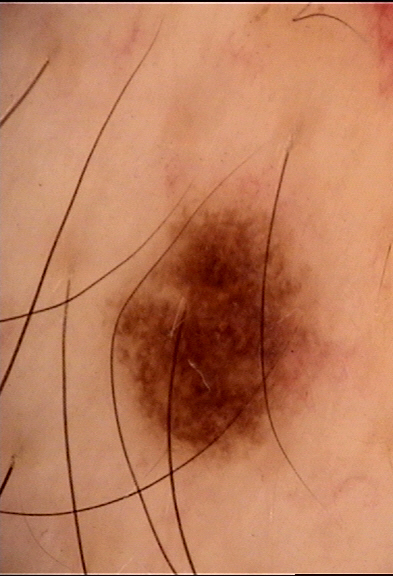Conclusion: The diagnosis was a dysplastic junctional nevus.